The contributor reports the lesion is fluid-filled and raised or bumpy. Present for less than one week. The photograph was taken at a distance. Male subject, age 18–29. The affected area is the arm and palm:
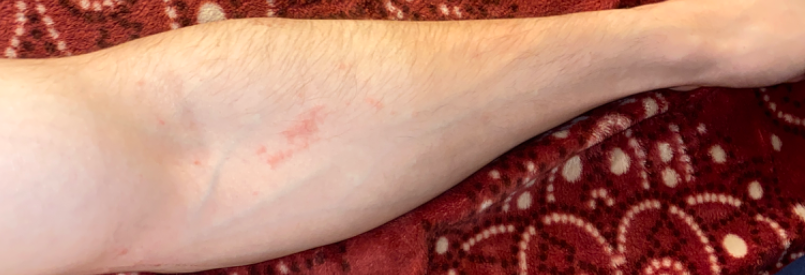On photographic review: Allergic Contact Dermatitis (67%); Eczema (33%).